A male subject, in their mid-70s. A dermoscopic close-up of a skin lesion:
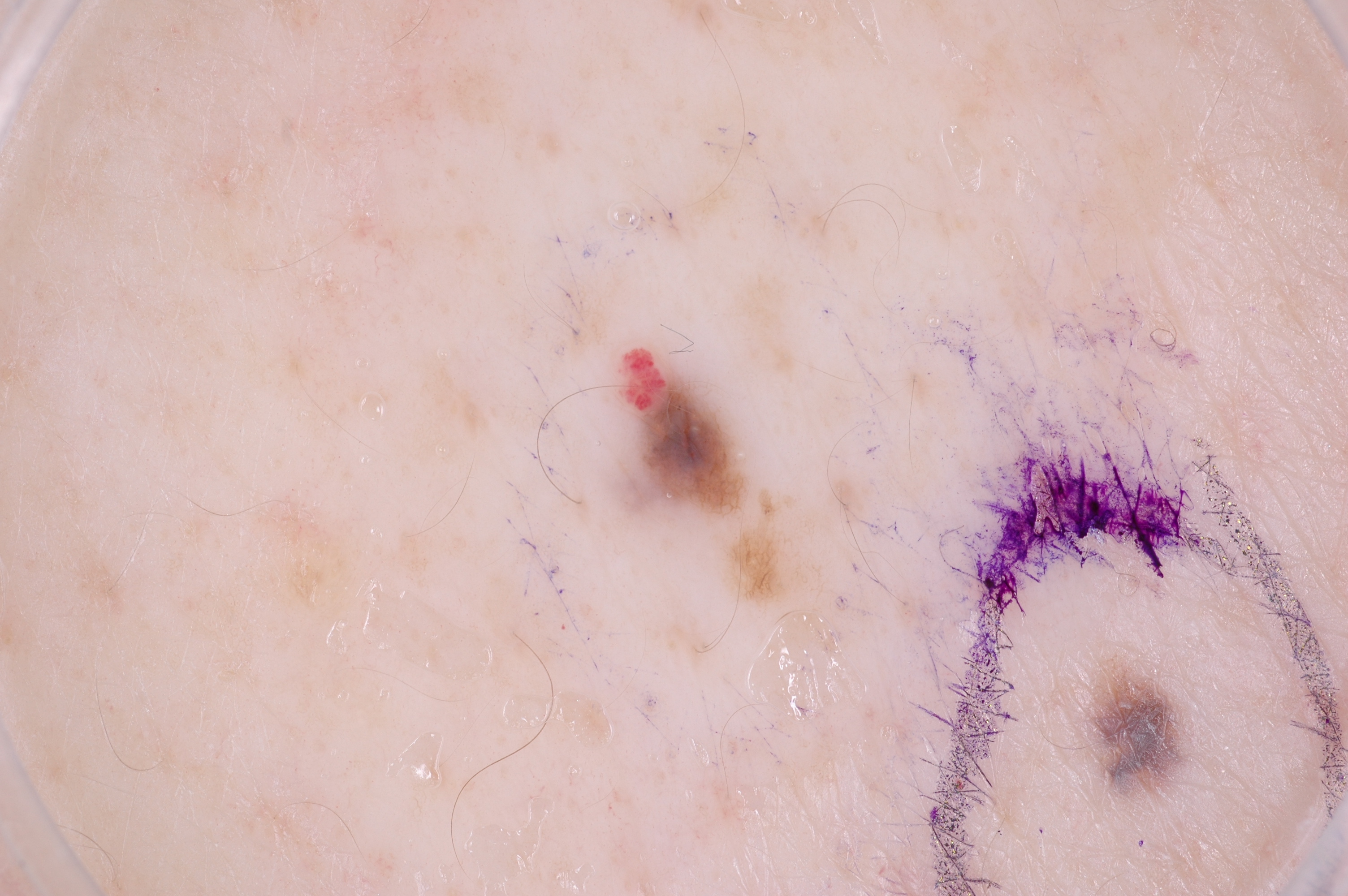Q: How large is the lesion within the image?
A: small
Q: What is the lesion's bounding box?
A: 633, 370, 751, 517
Q: What does dermoscopy show?
A: pigment network and milia-like cysts; absent: streaks and negative network
Q: What did the assessment conclude?
A: a melanocytic nevus, a benign lesion